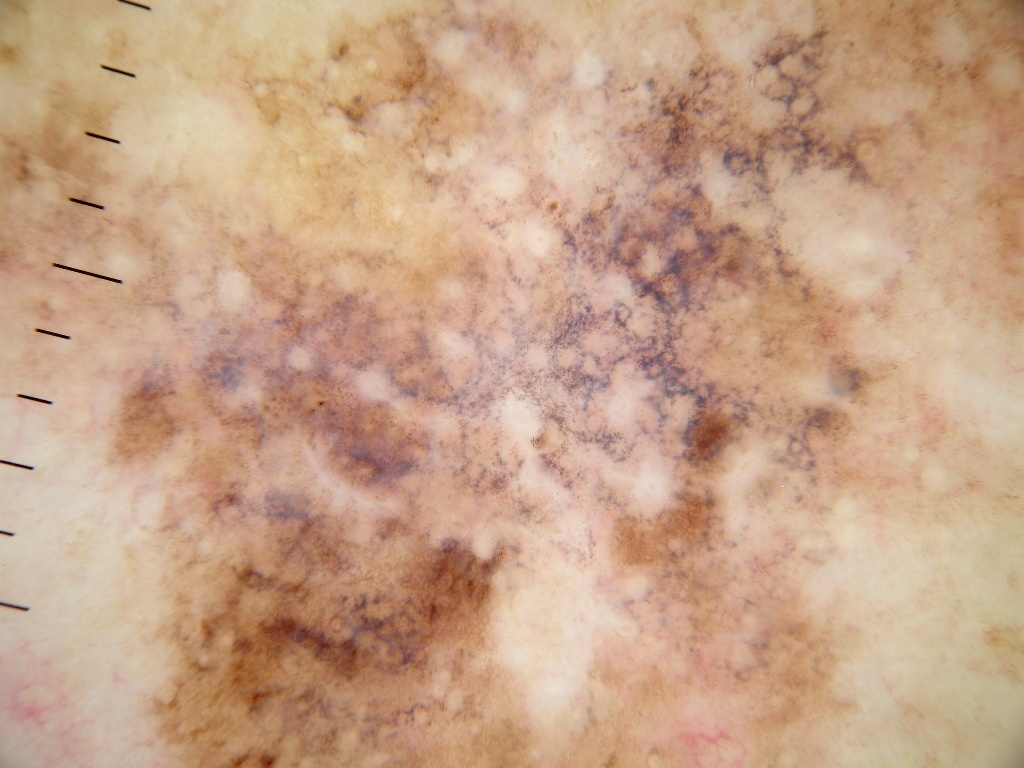Q: What is the imaging modality?
A: dermoscopy
Q: What is the lesion's bounding box?
A: extends across the entire field of view
Q: What is the diagnosis?
A: a malignant lesion